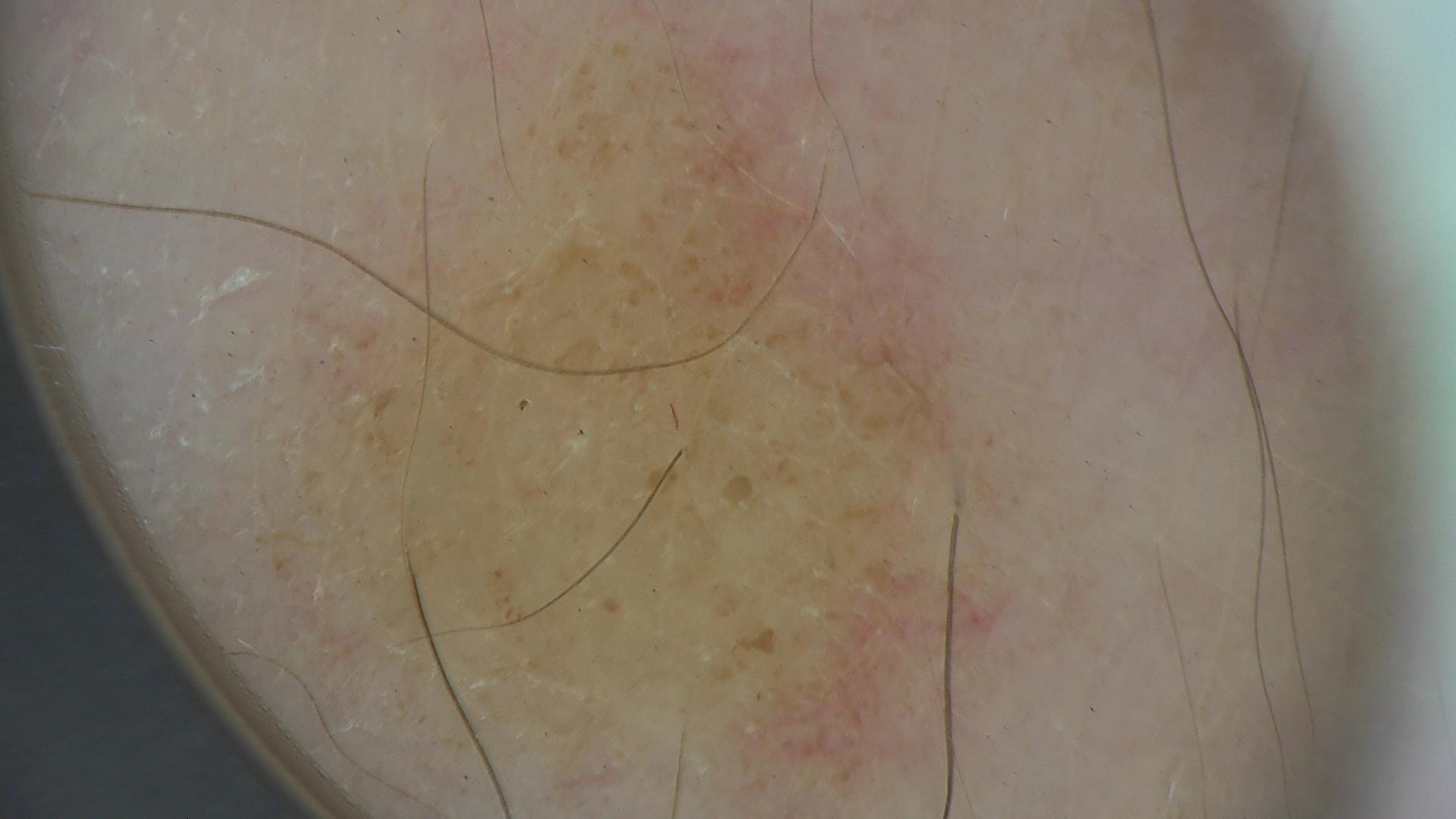Q: What is this lesion?
A: compound nevus (expert consensus)